A patient in their 40s.
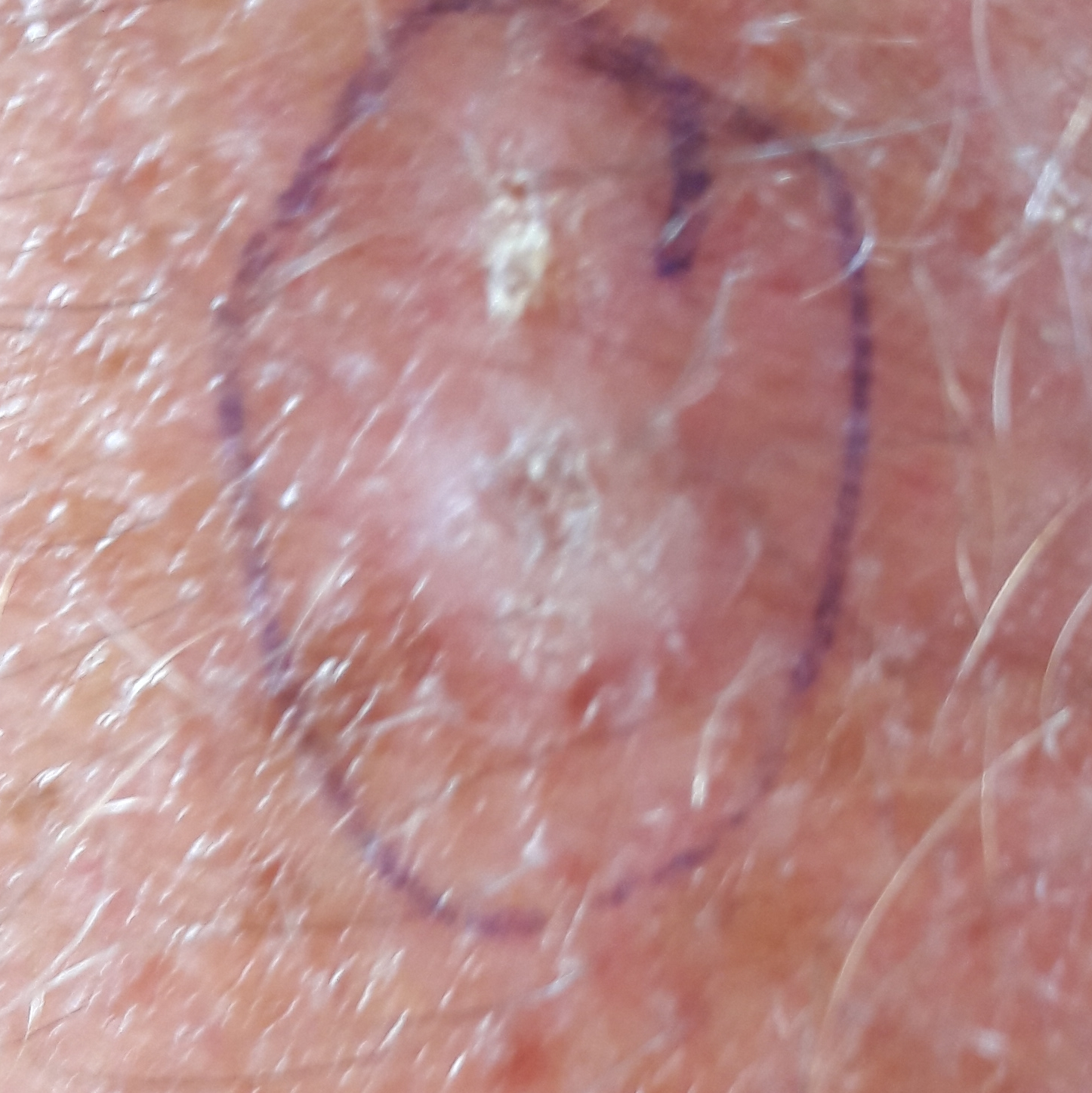Case summary:
The lesion involves a forearm. The patient reports that the lesion itches and is elevated, but has not bled.
Conclusion:
The consensus clinical diagnosis was an actinic keratosis.